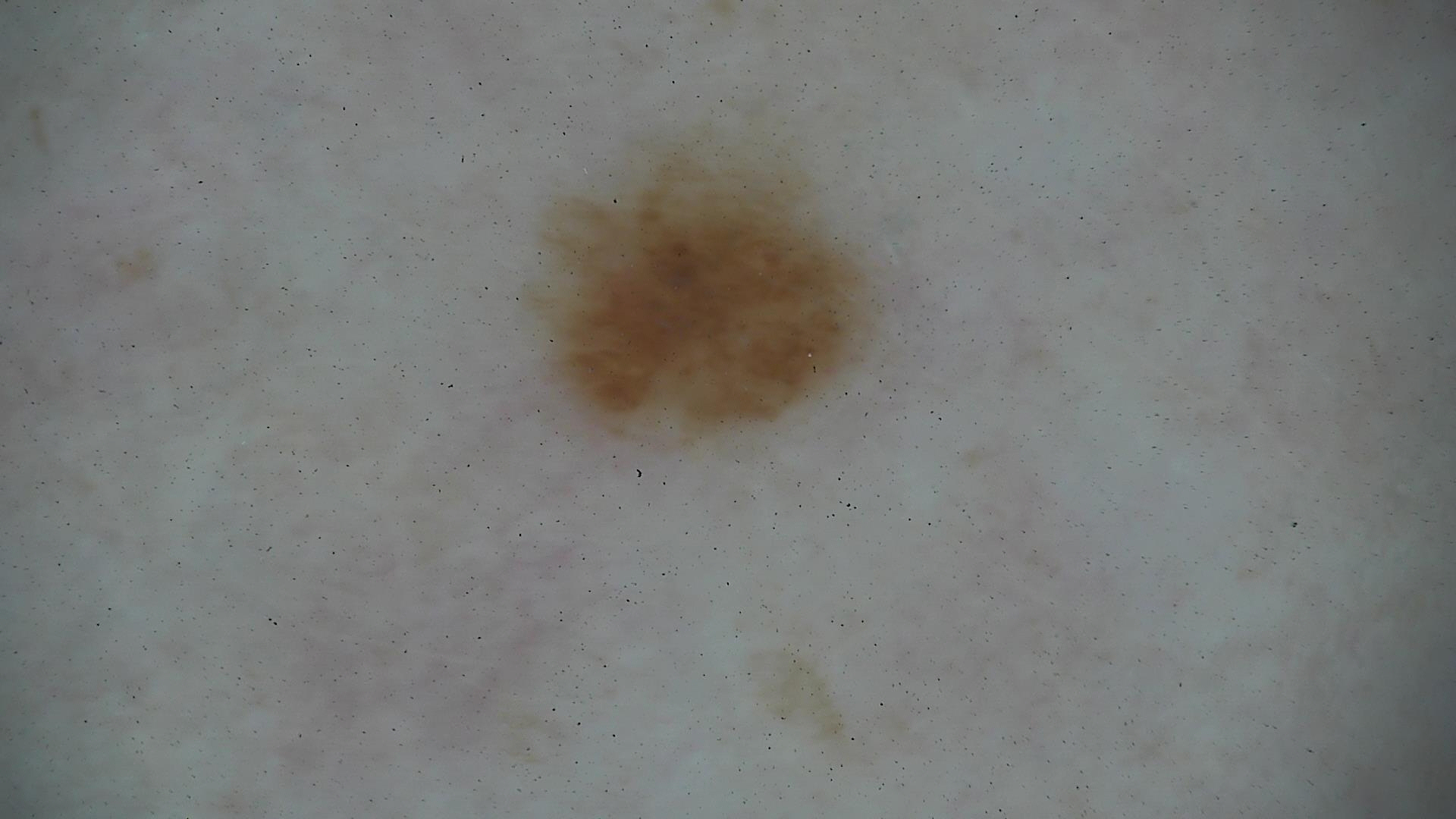diagnosis = dysplastic junctional nevus (expert consensus).